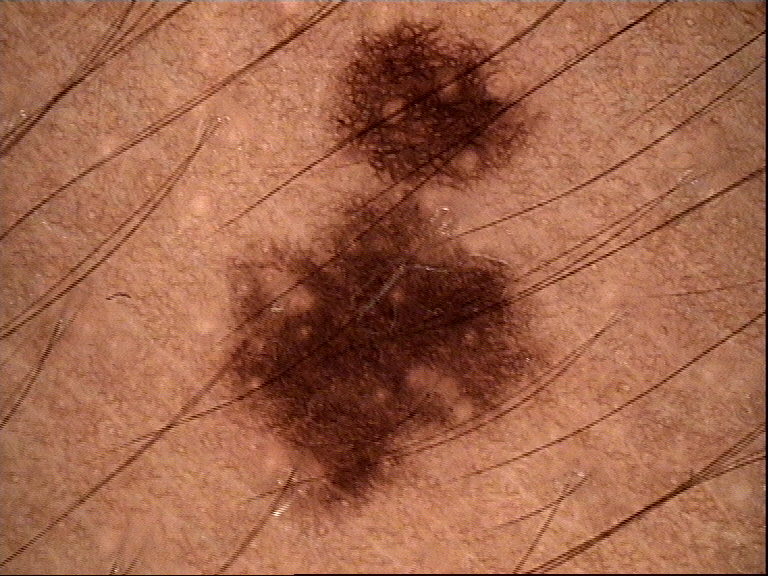modality: dermatoscopy
diagnosis: dysplastic junctional nevus (expert consensus)